An image taken at an angle:
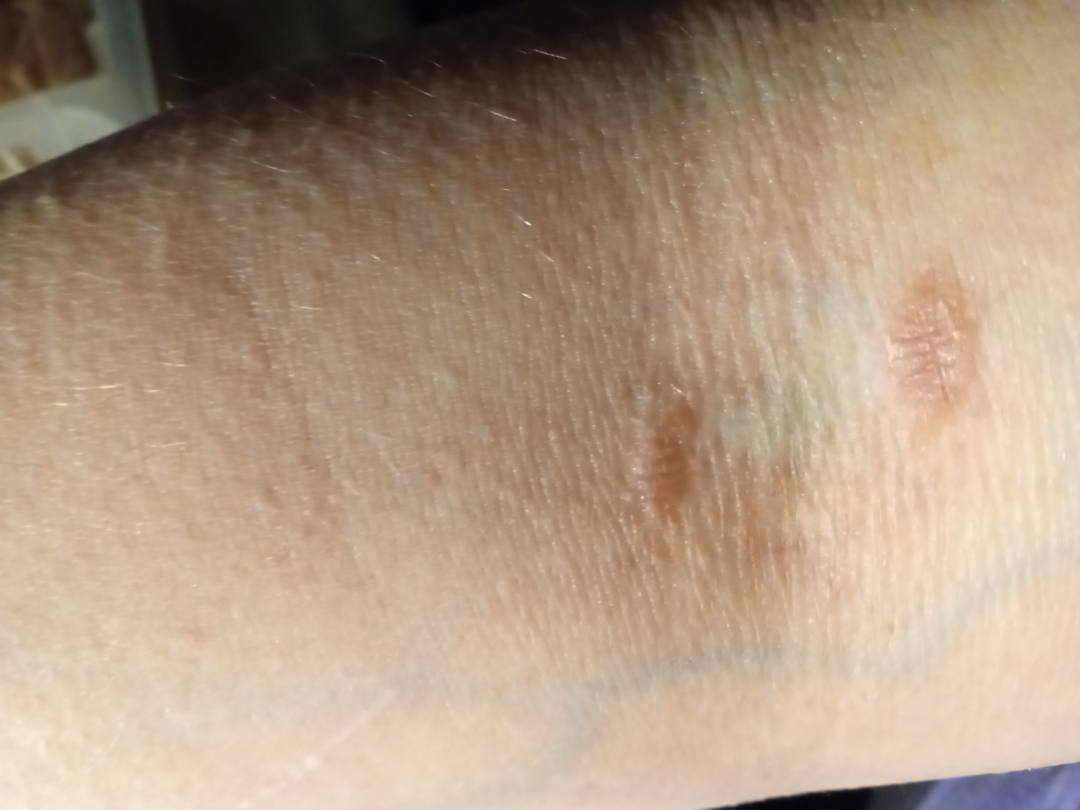The skin condition could not be confidently assessed from this image.